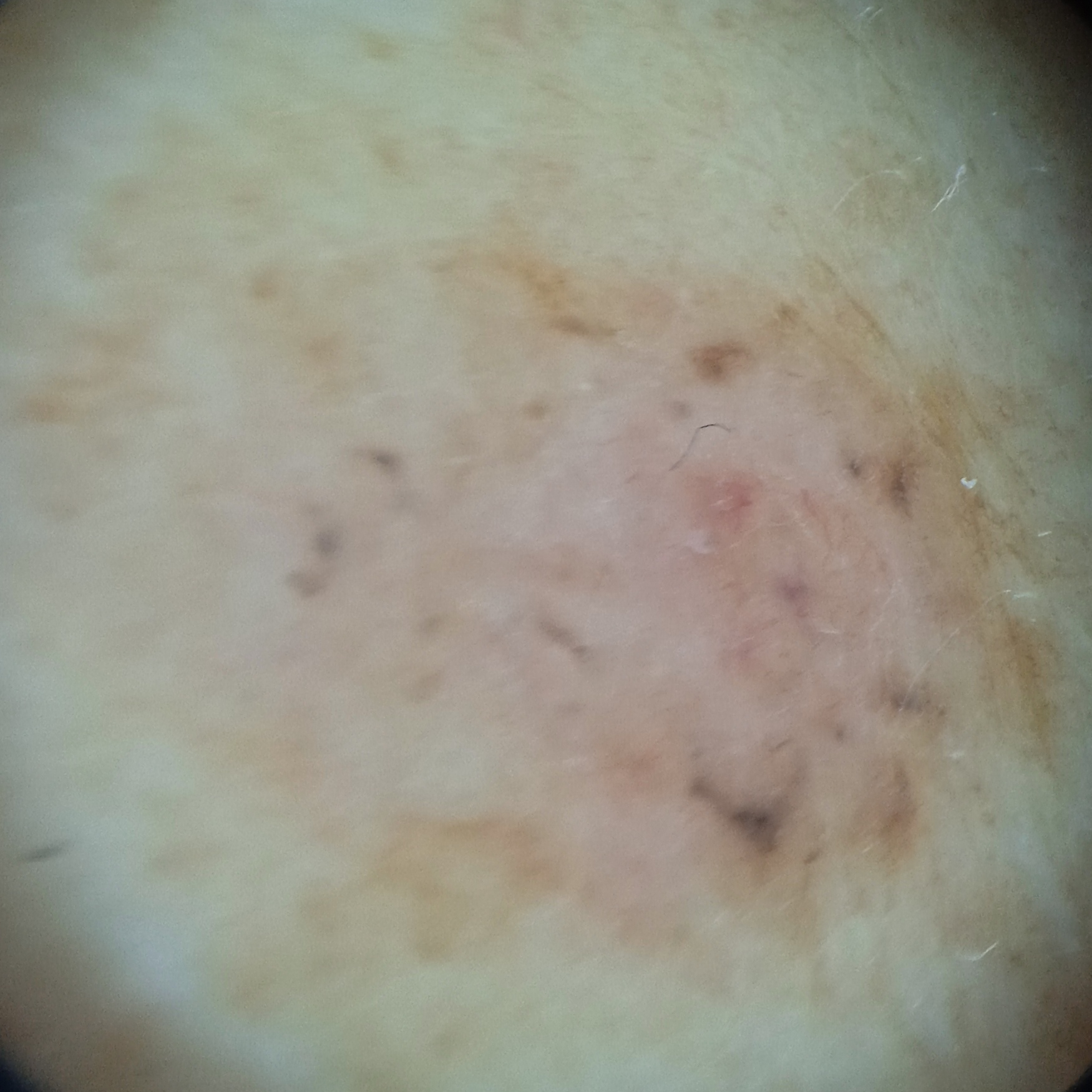clinical context: clinical suspicion of basal cell carcinoma | patient: female, 64 years of age | image: dermatoscopic image | diameter: 9.8 mm | pathology: basal cell carcinoma (biopsy-proven).